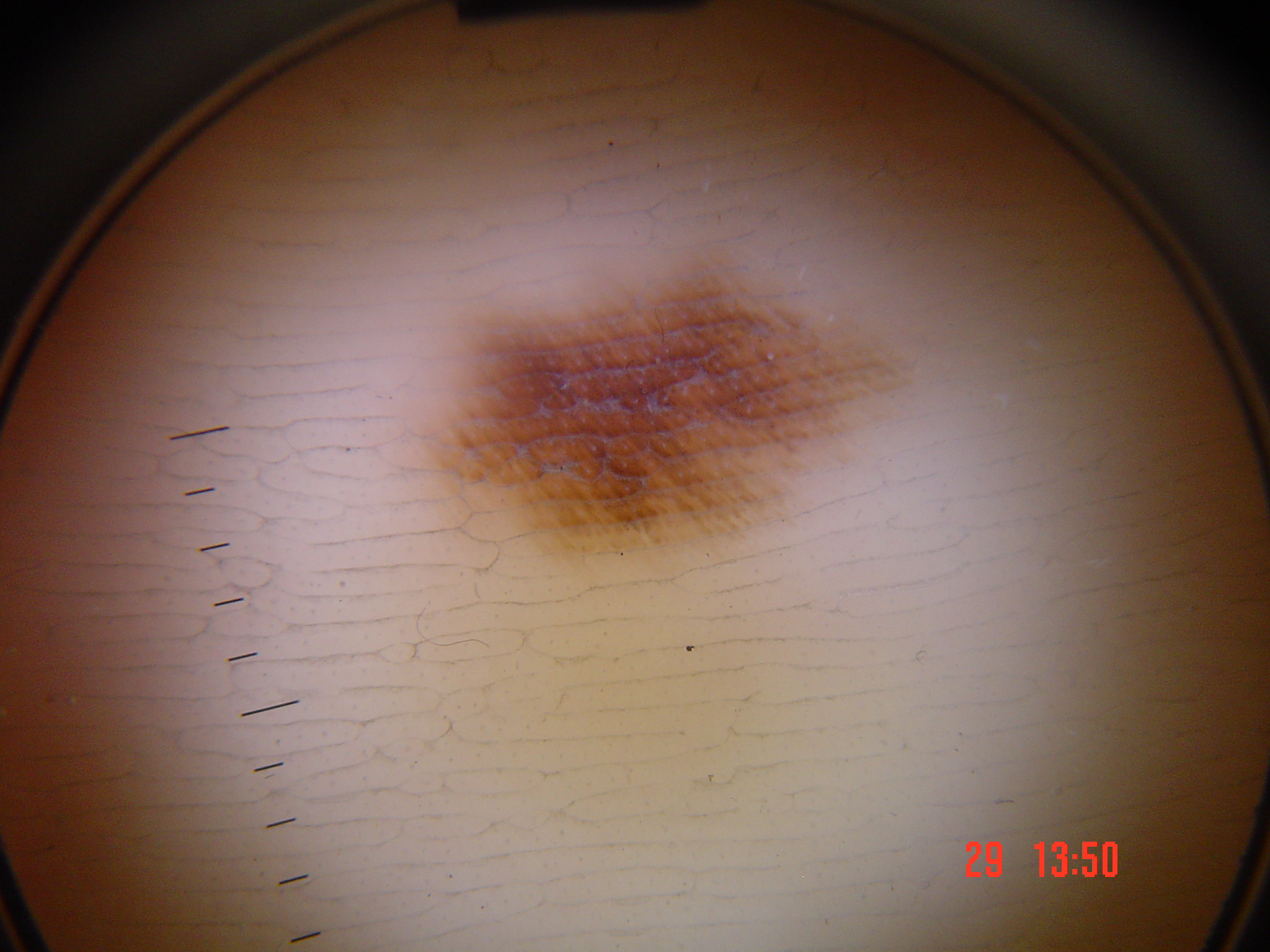A skin lesion imaged with a dermatoscope.
The diagnostic label was a benign lesion — an acral dysplastic junctional nevus.